The photo was captured at an angle.
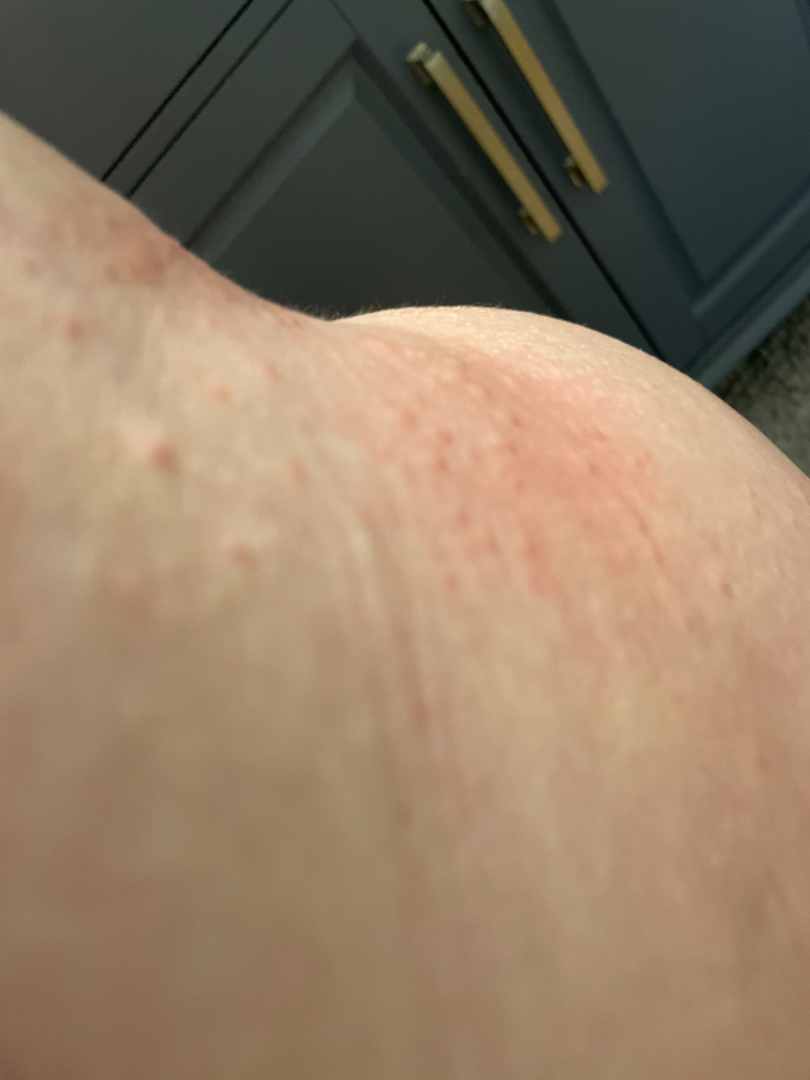Insect Bite and Allergic Contact Dermatitis were considered with similar weight; less likely is Urticaria.